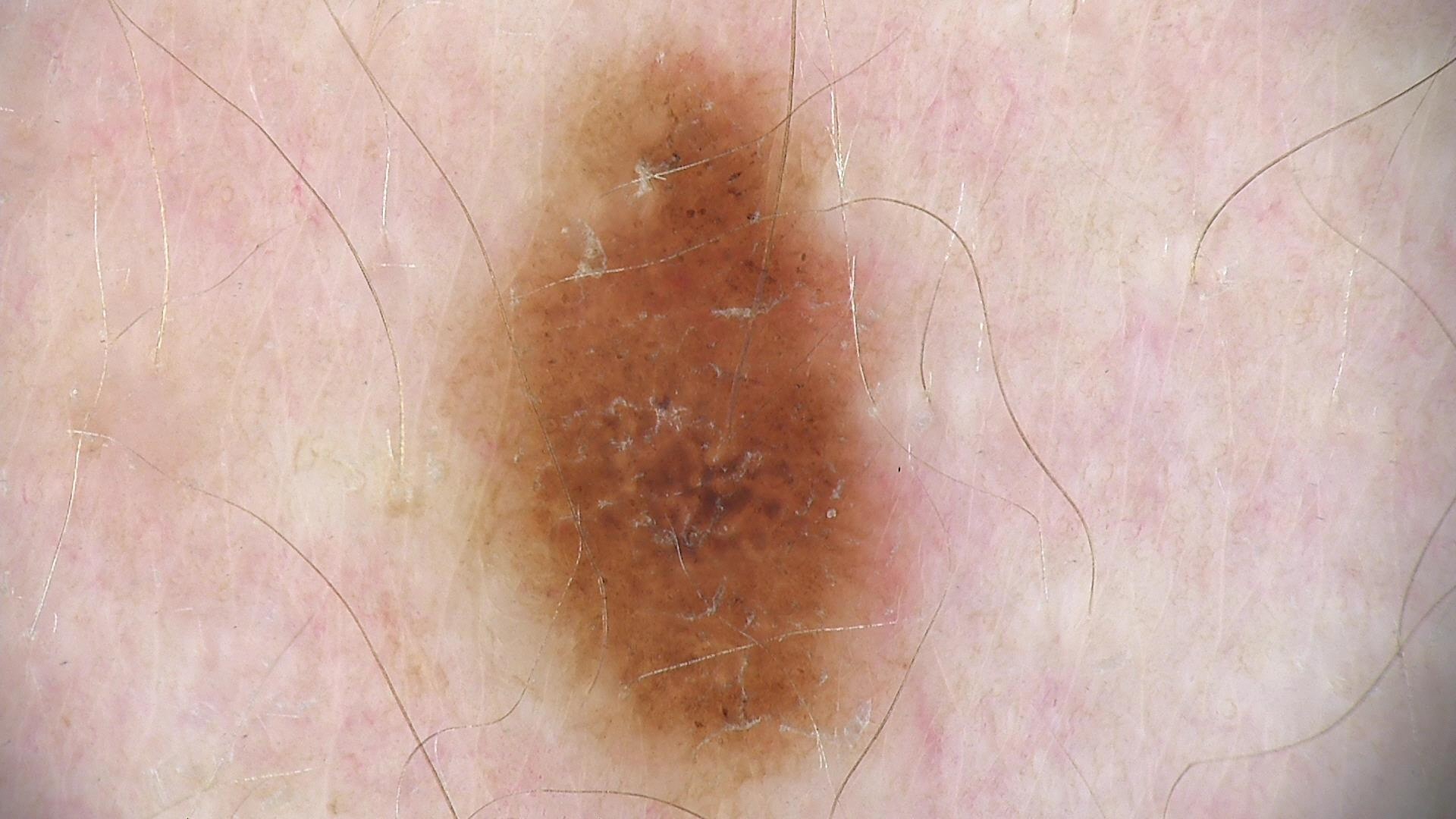Consistent with a compound nevus.